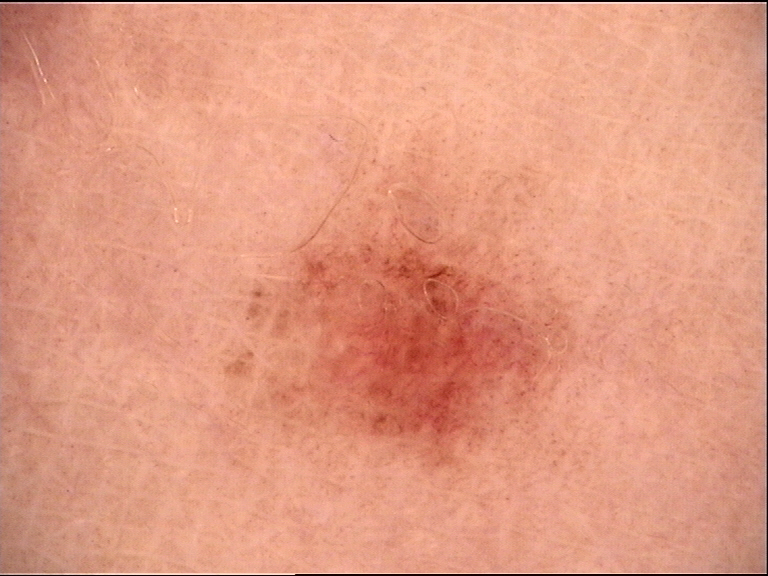The diagnostic label was a dysplastic junctional nevus.